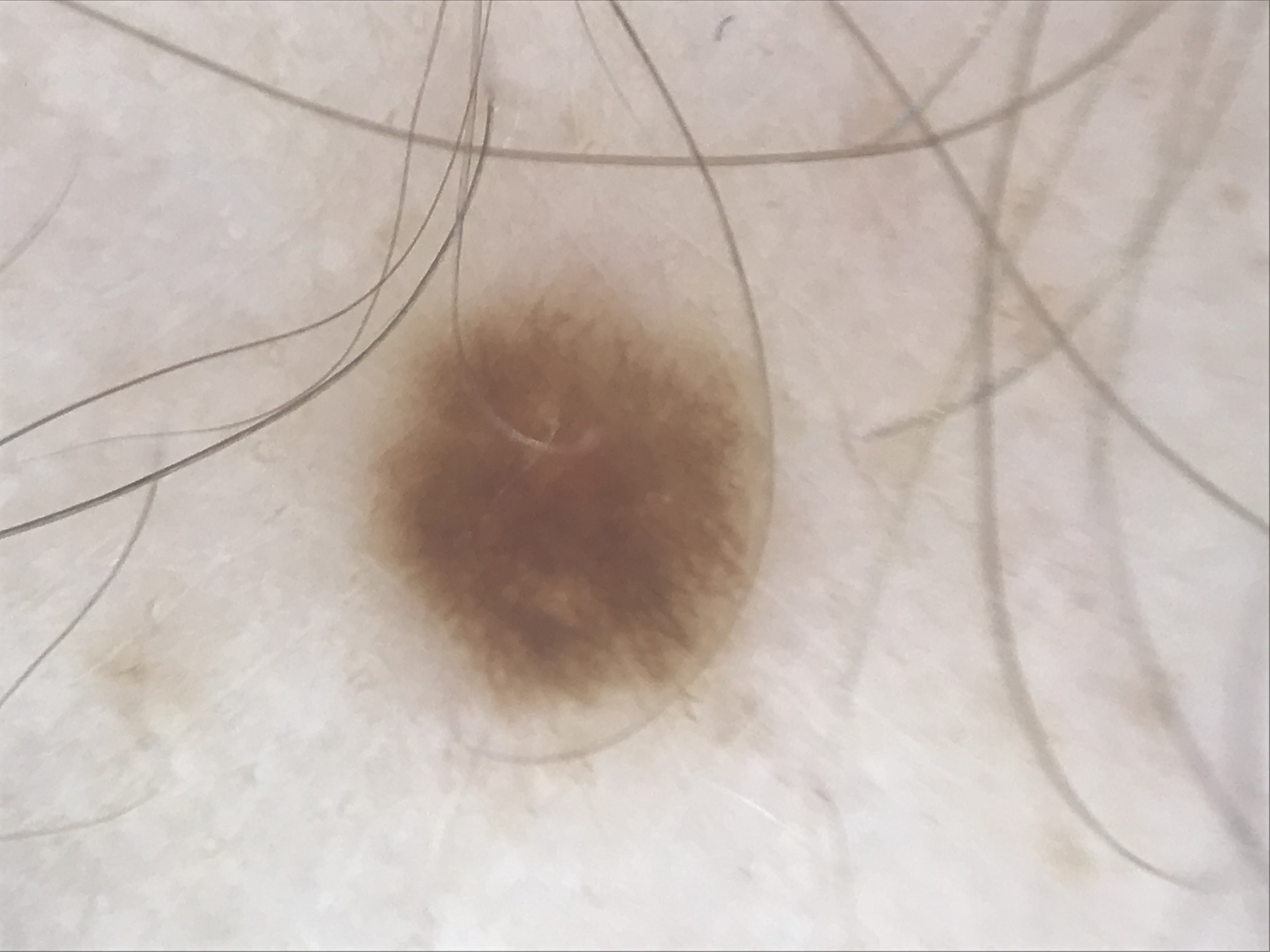Q: What is the diagnosis?
A: junctional nevus (expert consensus)